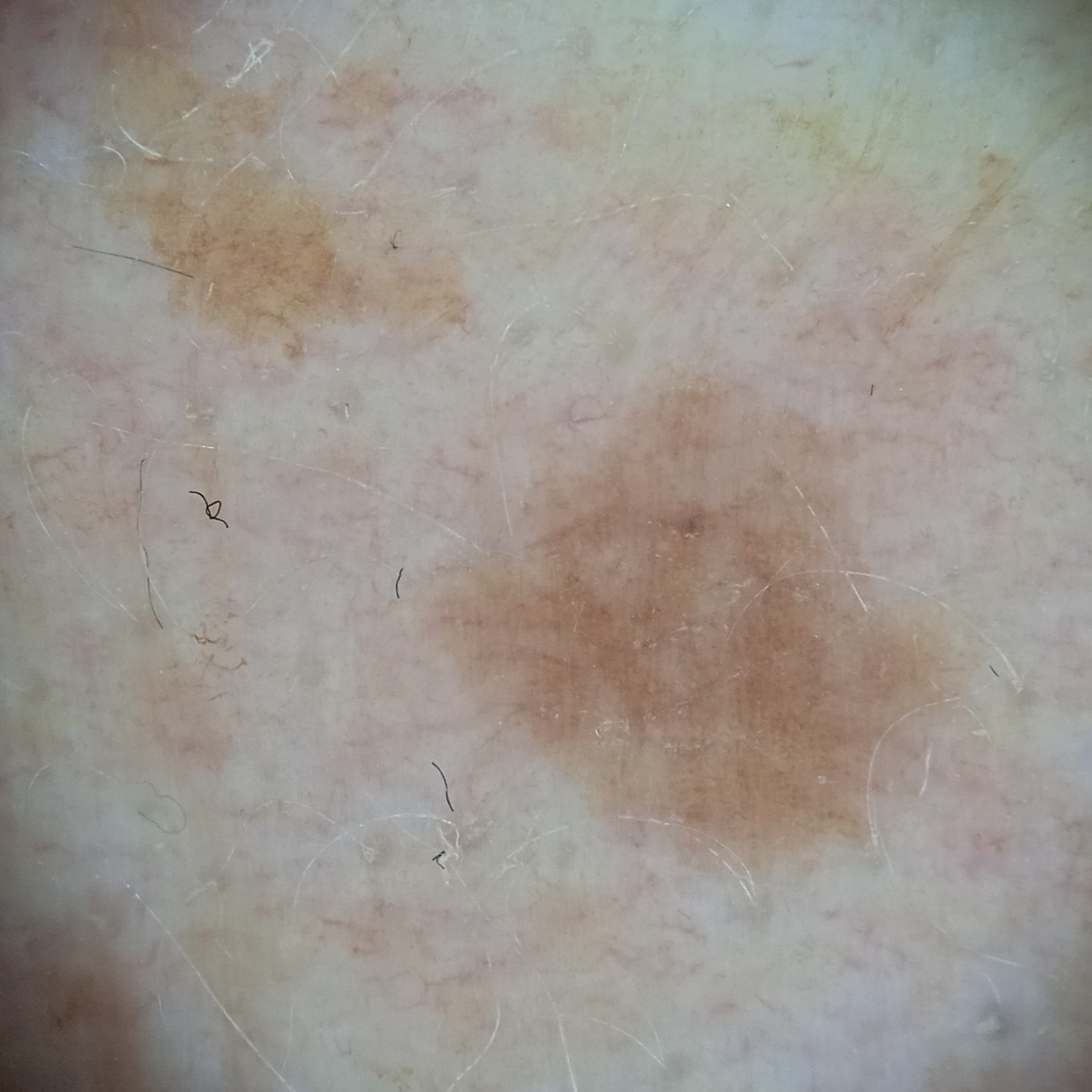nevus count: a moderate number of melanocytic nevi | referral: research study (no referral diagnosis) | patient: female, aged 59 | sun reaction: skin reddens with sun exposure | image type: dermoscopic image | site: an arm | diagnosis: melanocytic nevus (dermatologist consensus).